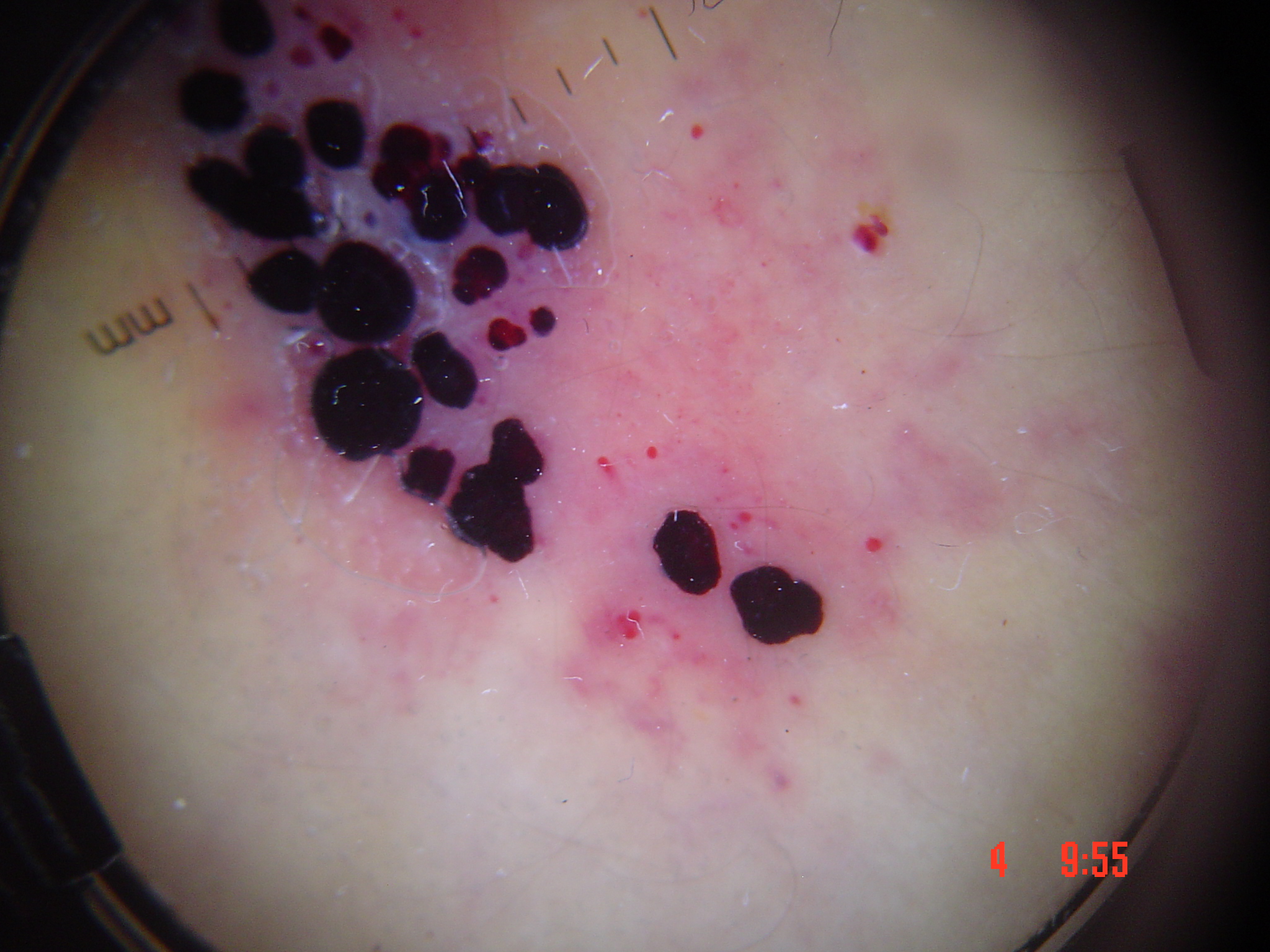assessment — angiokeratoma (expert consensus)